A close-up photograph. The lesion involves the leg — 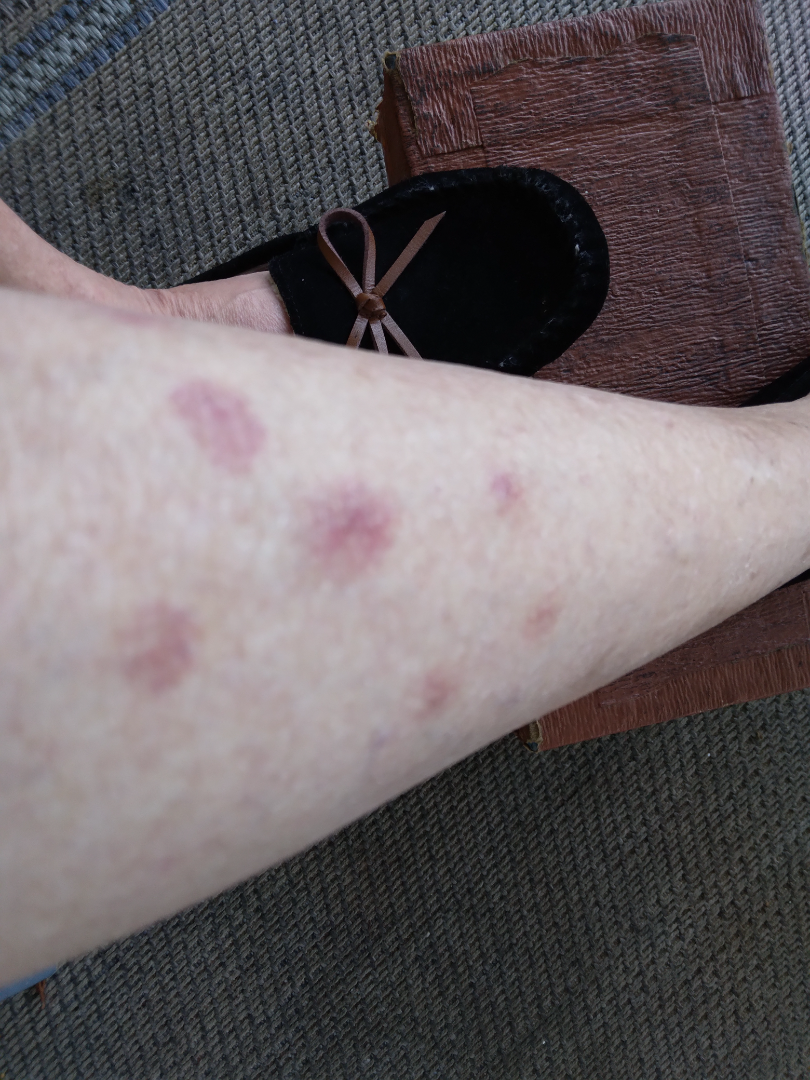• assessment · not assessable
• skin tone · FST III
• texture · flat
• symptom duration · about one day